Dermoscopy of a skin lesion.
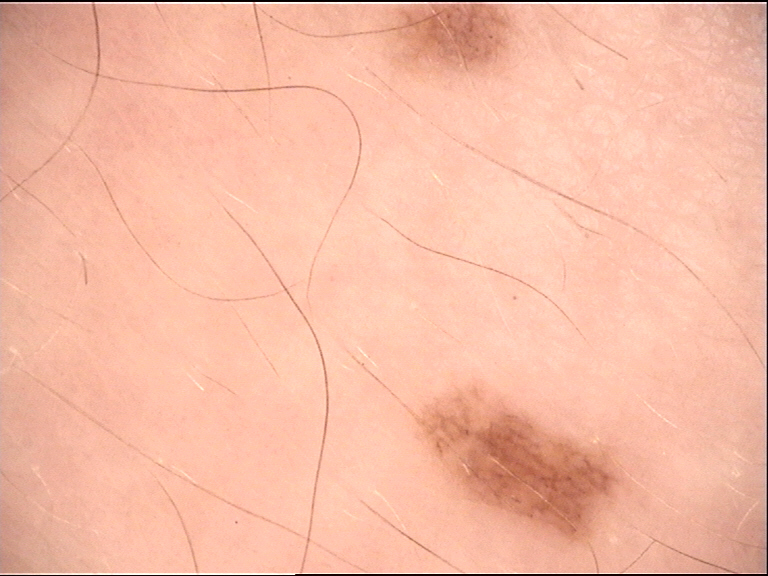Conclusion:
Consistent with a benign lesion — a dysplastic junctional nevus.